A male patient age 69 · a clinical photograph of a skin lesion:
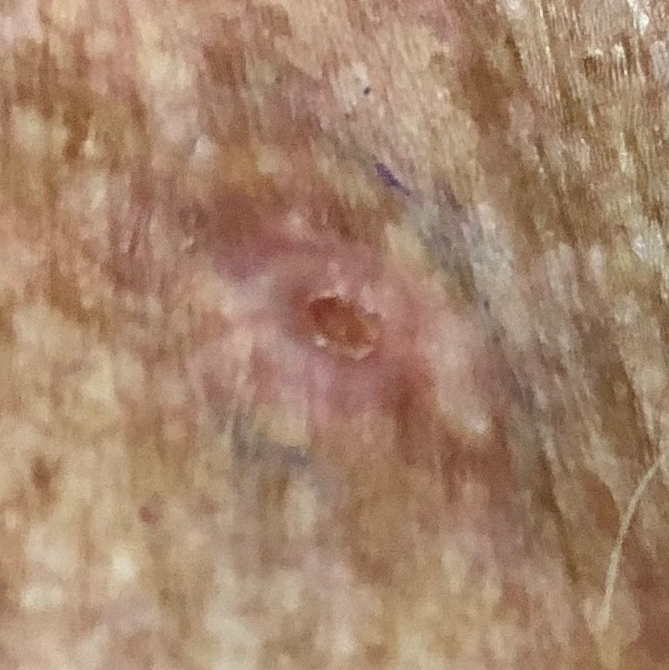The lesion was found on the chest.
The patient reports that the lesion is elevated, itches, has bled, and hurts.
Histopathological examination showed a basal cell carcinoma.